A female patient 59 years old. Referred with a clinical suspicion of melanocytic nevus. A dermoscopic image of a skin lesion:
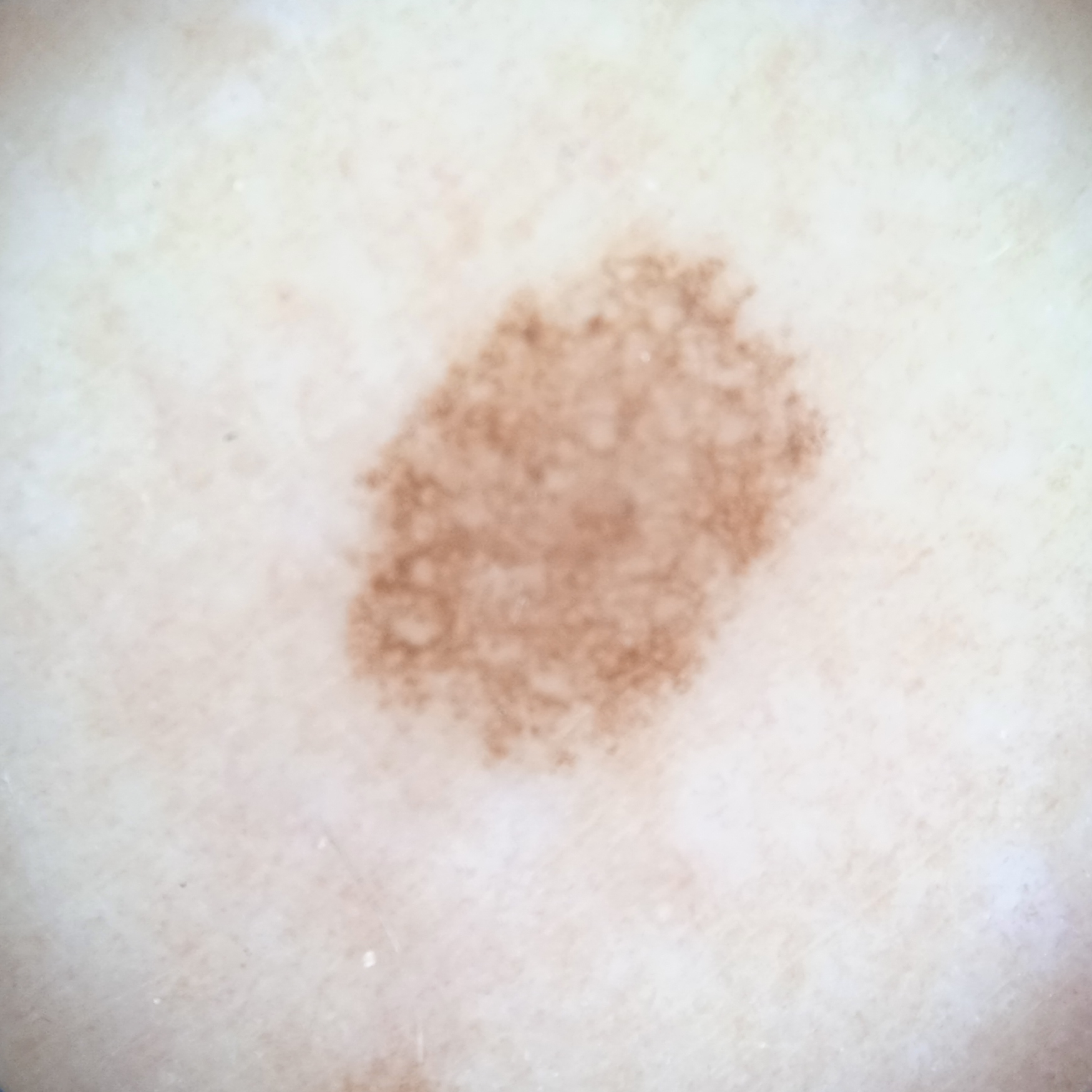<lesion>
<lesion_location>an arm</lesion_location>
<lesion_size>
<diameter_mm>6.7</diameter_mm>
</lesion_size>
<diagnosis>
<name>atypical (dysplastic) nevus</name>
<malignancy>benign</malignancy>
<procedure>excision</procedure>
</diagnosis>
</lesion>